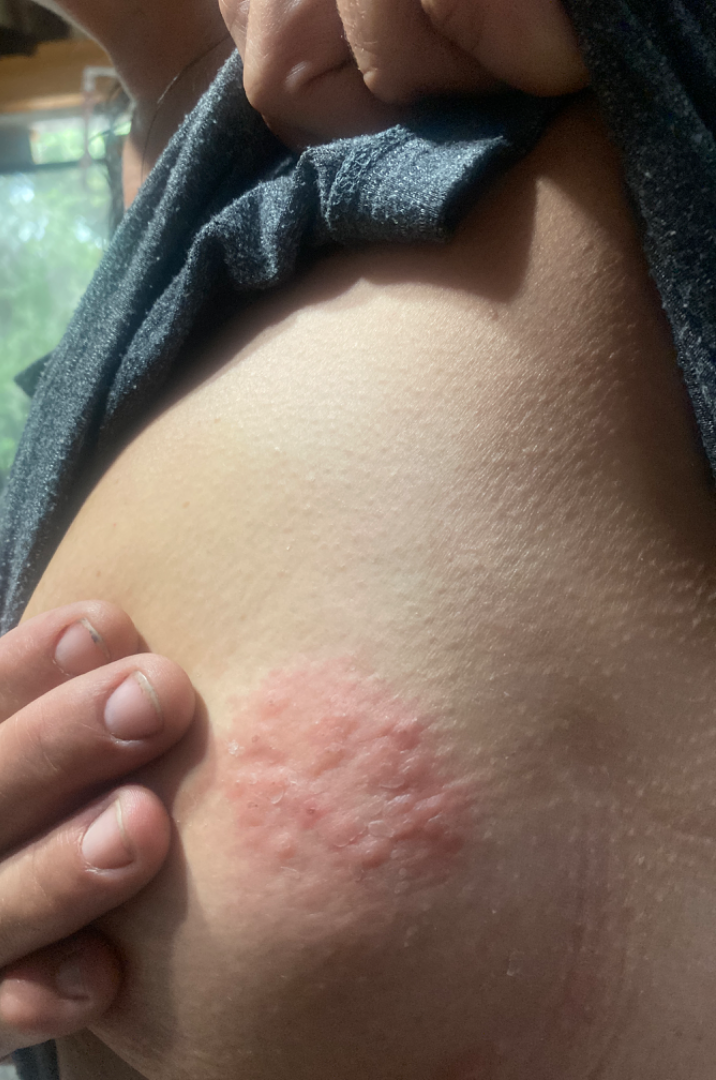The dermatologist could not determine a likely condition from the photograph alone. Skin tone: Fitzpatrick II. The affected area is the back of the torso and front of the torso. Present for less than one week. The lesion is associated with bothersome appearance, itching and enlargement. Female subject, age 50–59. Texture is reported as raised or bumpy. The photograph is a close-up of the affected area.